Present for one to three months. The patient considered this a rash. Reported lesion symptoms include burning and itching. Associated systemic symptoms include shortness of breath and mouth sores. The contributor is a female aged 40–49. The arm, front of the torso, head or neck and palm are involved. The lesion is described as raised or bumpy and rough or flaky. The photograph was taken at a distance:
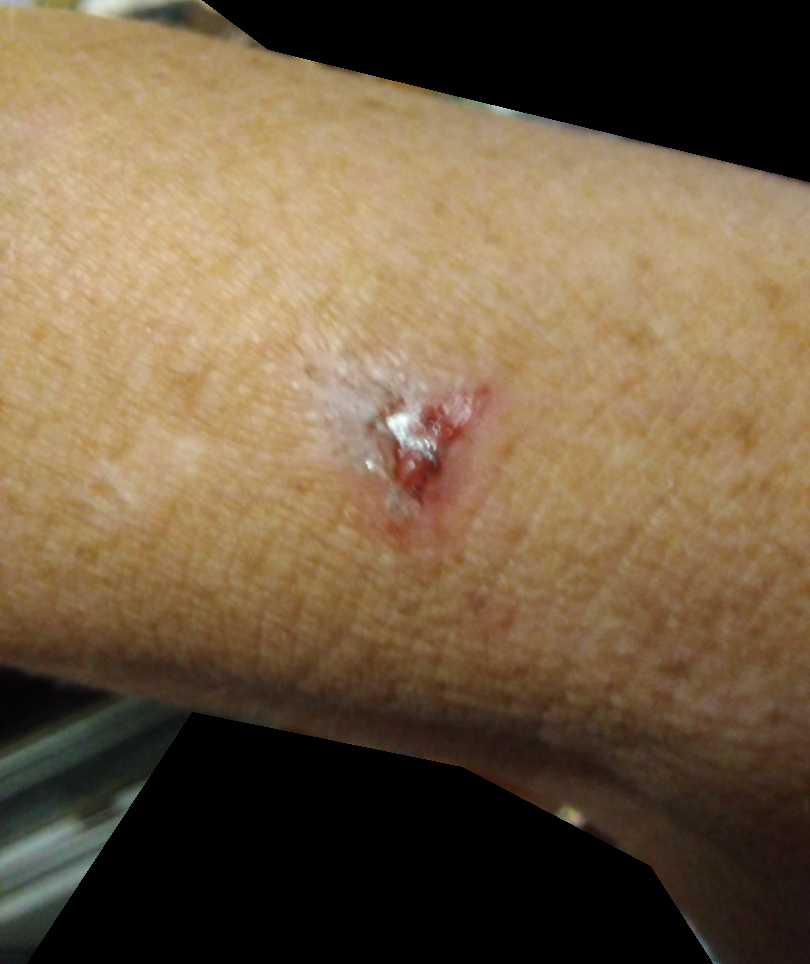The skin condition could not be confidently assessed from this image.